A clinical photograph showing a skin lesion:
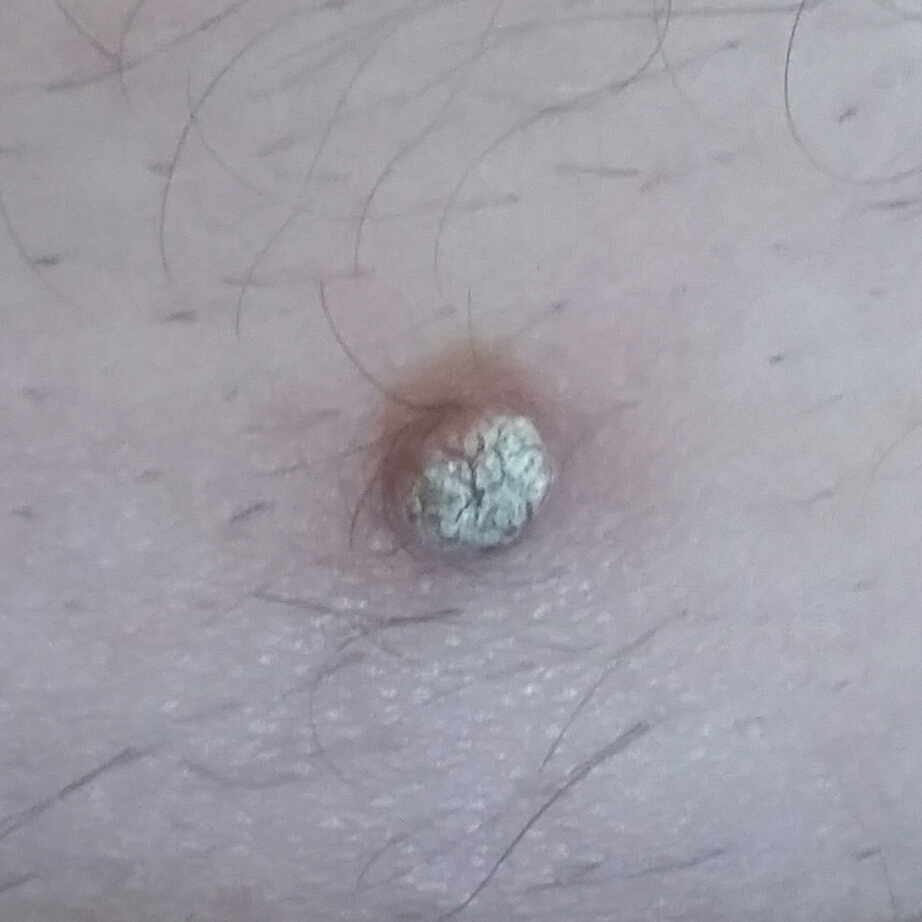The lesion involves the abdomen. The lesion measures 5 × 5 mm. Histopathologically confirmed as an actinic keratosis.